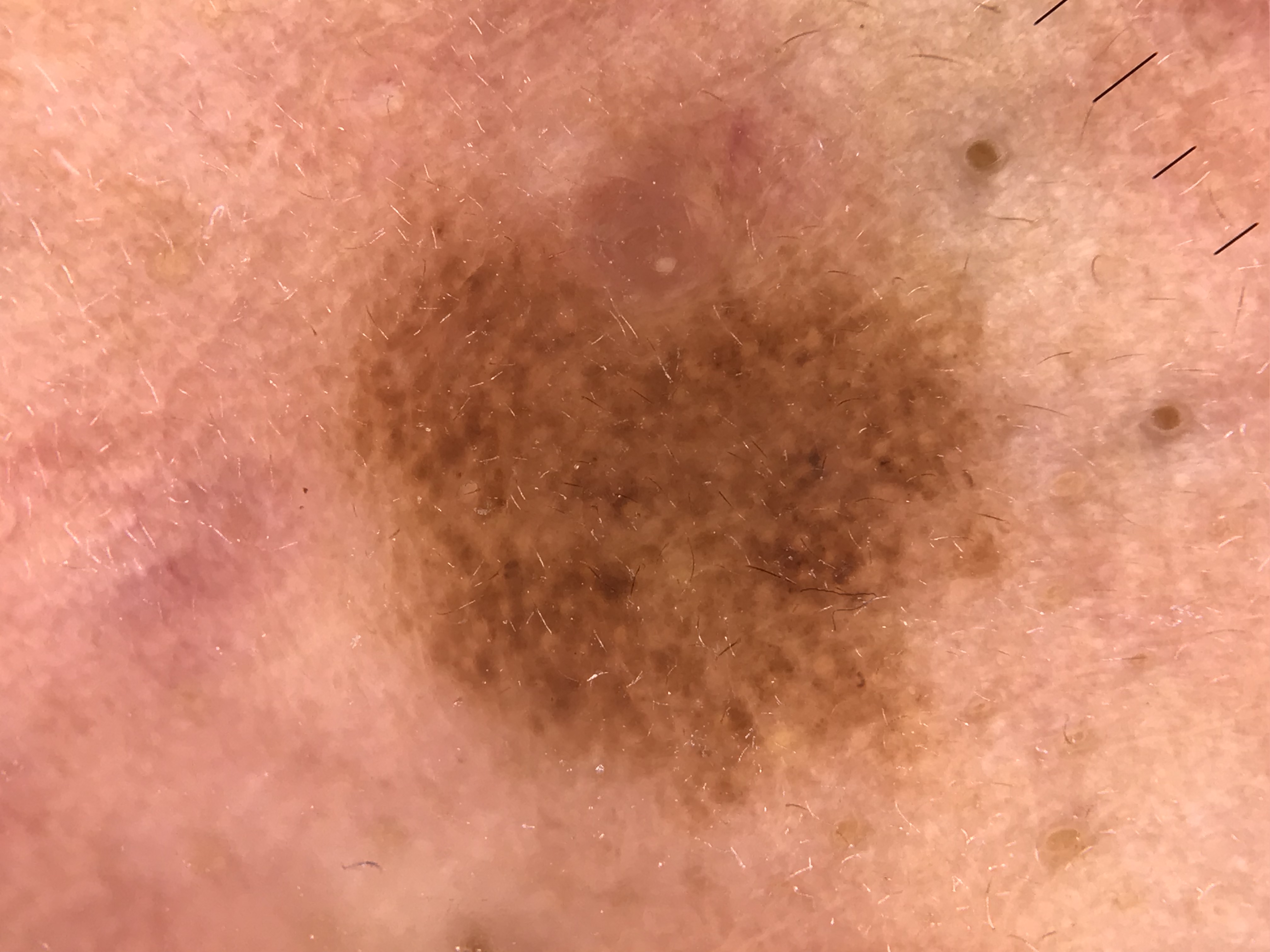- diagnostic label · compound nevus (expert consensus)